FST II · by history, prior malignancy (patient or family), no pesticide exposure, and no tobacco use · a female subject age 36: 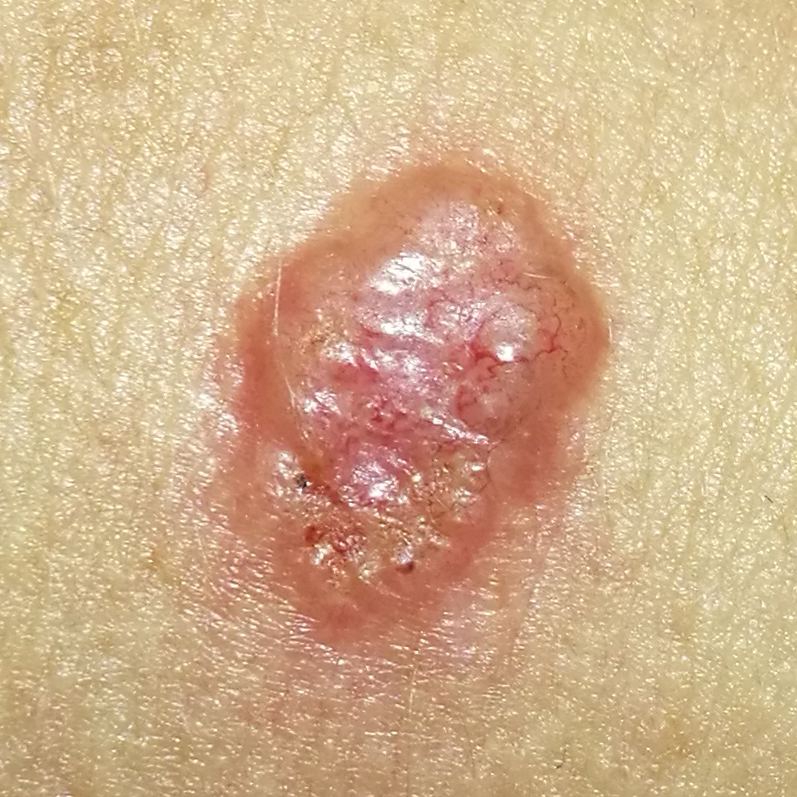Case summary: The lesion measures approximately 15 × 10 mm. The patient describes that the lesion hurts, has bled, itches, has grown, and is elevated, but has not changed. Conclusion: Histopathological examination showed a basal cell carcinoma.